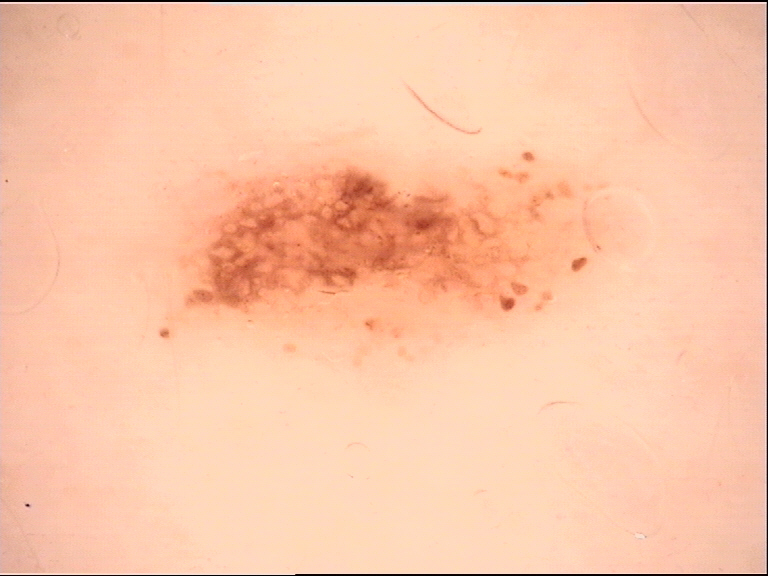Findings:
A dermoscopy image of a single skin lesion.
Conclusion:
The diagnostic label was a benign lesion — a dysplastic junctional nevus.